A dermatoscopic image of a skin lesion:
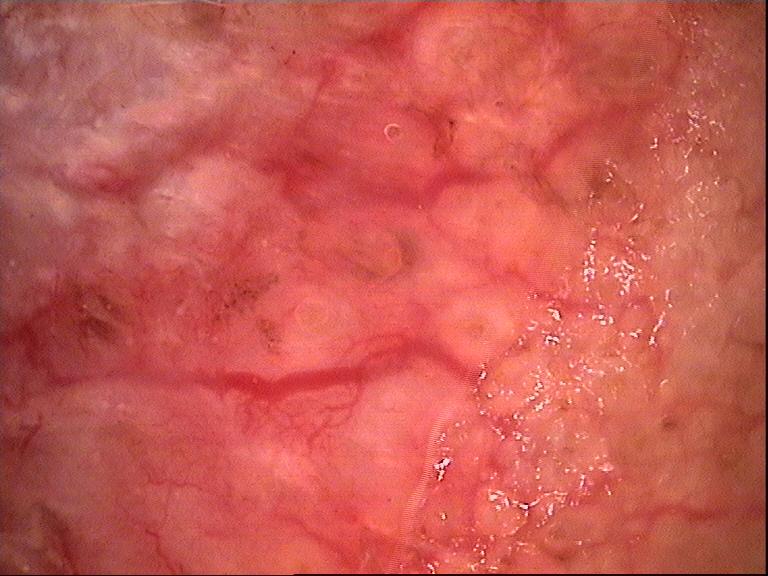Case: The morphology is that of a keratinocytic lesion. Conclusion: The biopsy diagnosis was a basal cell carcinoma.